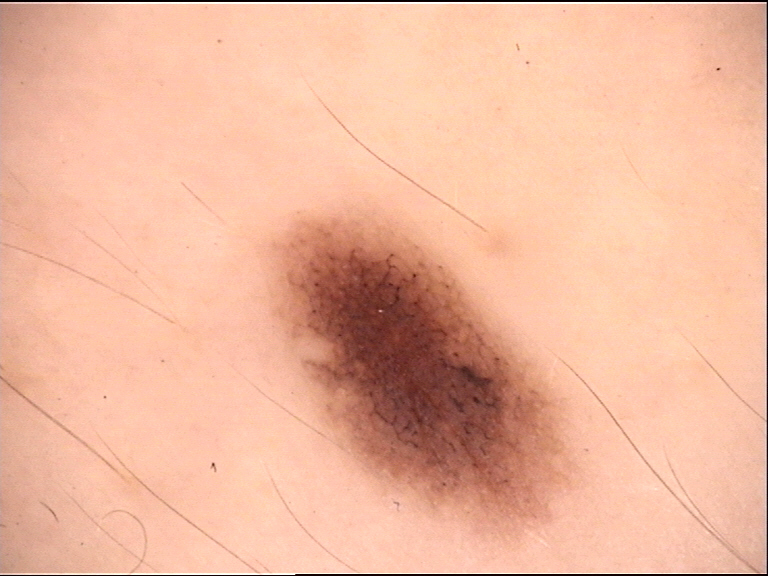Case:
• imaging · dermoscopy
• diagnostic label · dysplastic junctional nevus (expert consensus)